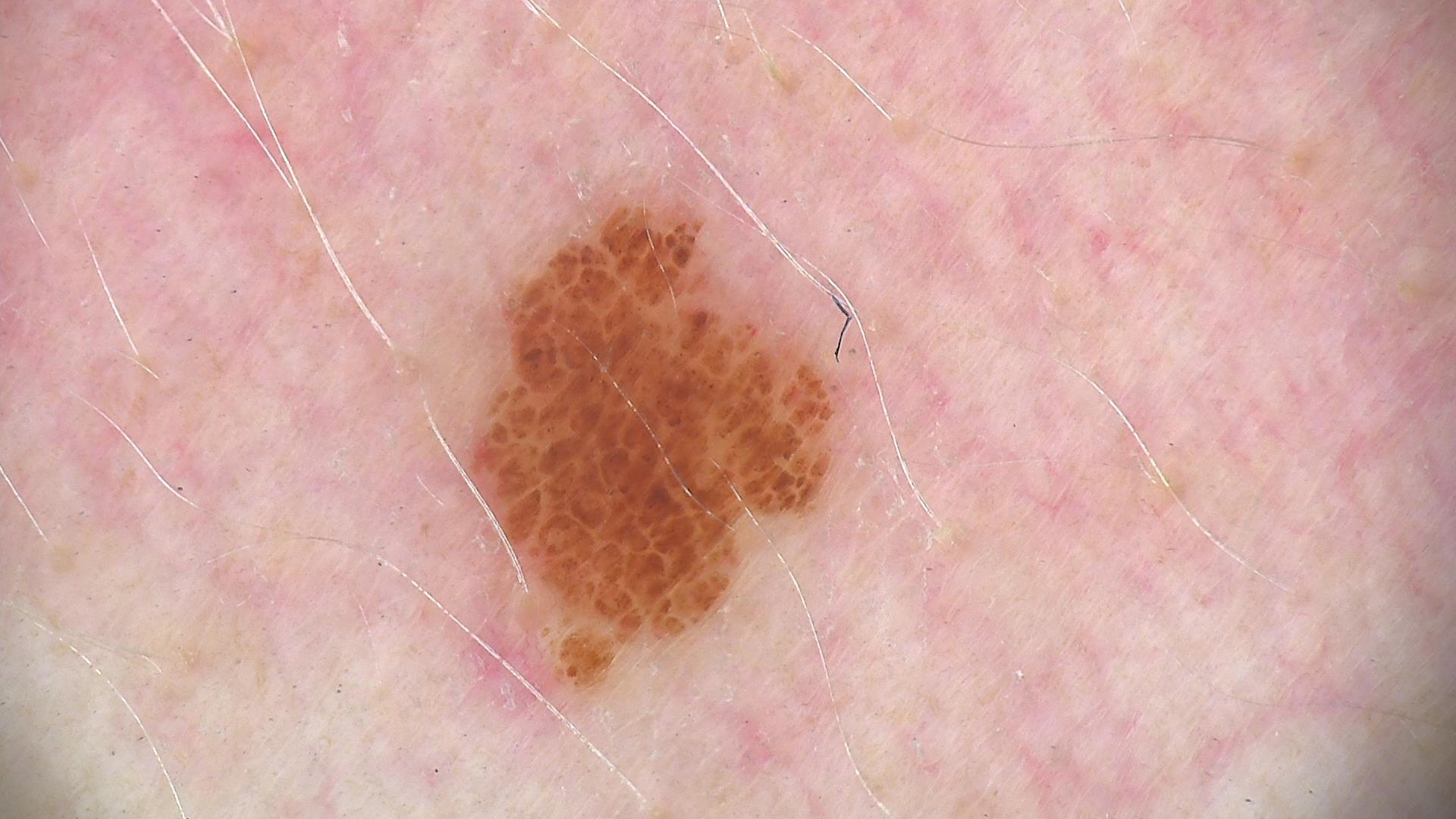Case: A dermatoscopic image of a skin lesion. This is a banal lesion. Impression: Classified as a junctional nevus.